The leg is involved, the photo was captured at a distance: 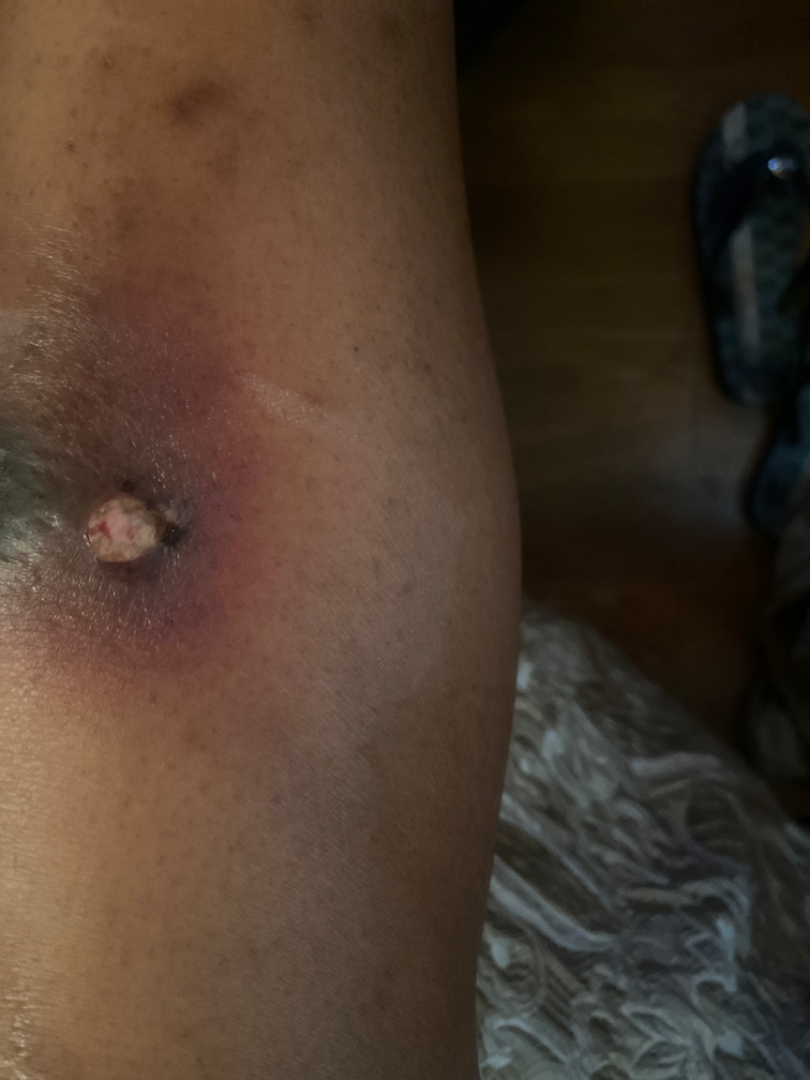{
  "assessment": "ungradable on photographic review"
}